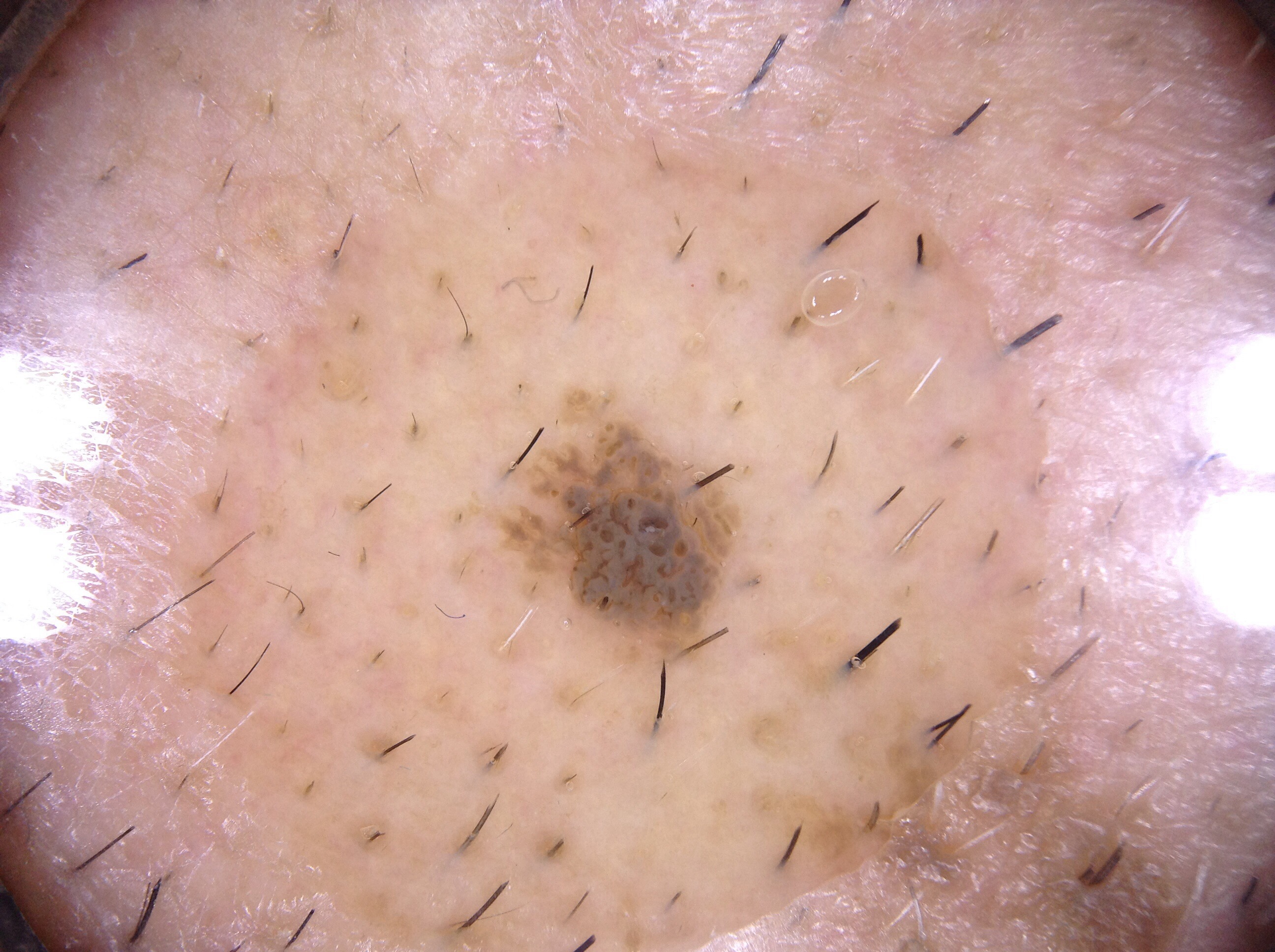A male subject, aged approximately 60. A skin lesion imaged with a dermatoscope. With coordinates (x1, y1, x2, y2), the lesion's extent is 529/432/737/639. Dermoscopy demonstrates no pigment network, milia-like cysts, negative network, or streaks. The lesion was assessed as a seborrheic keratosis, a benign lesion.